A dermoscopy image of a single skin lesion — 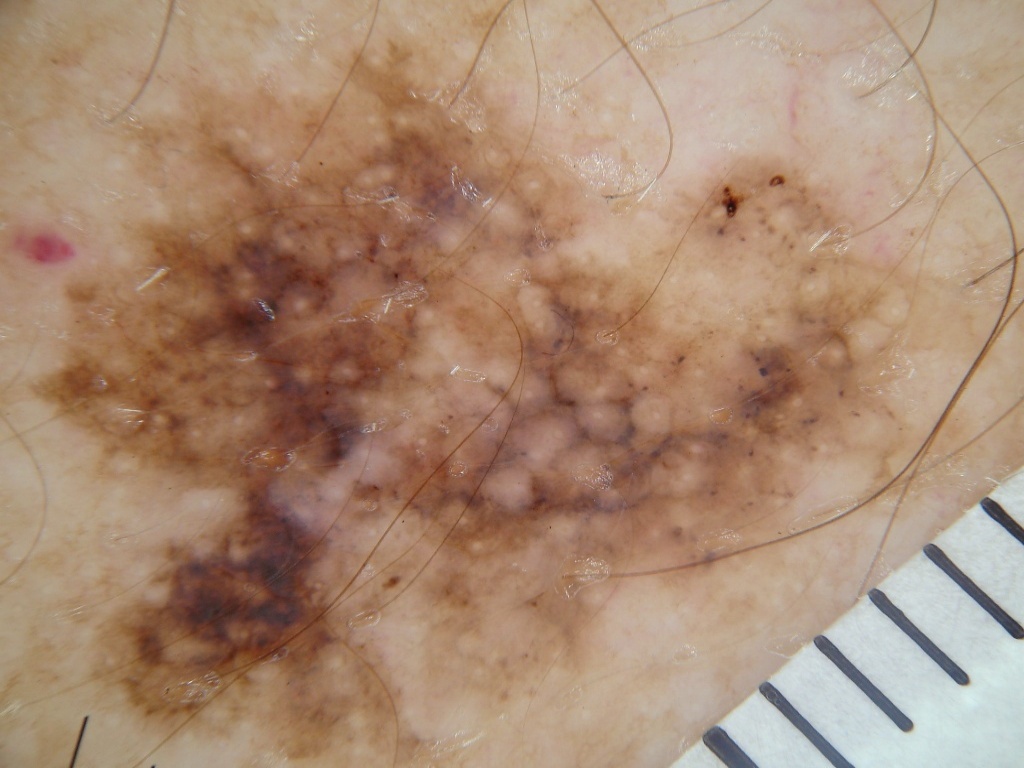lesion location: [21,34,945,766] | diagnosis: a melanoma, a malignancy.